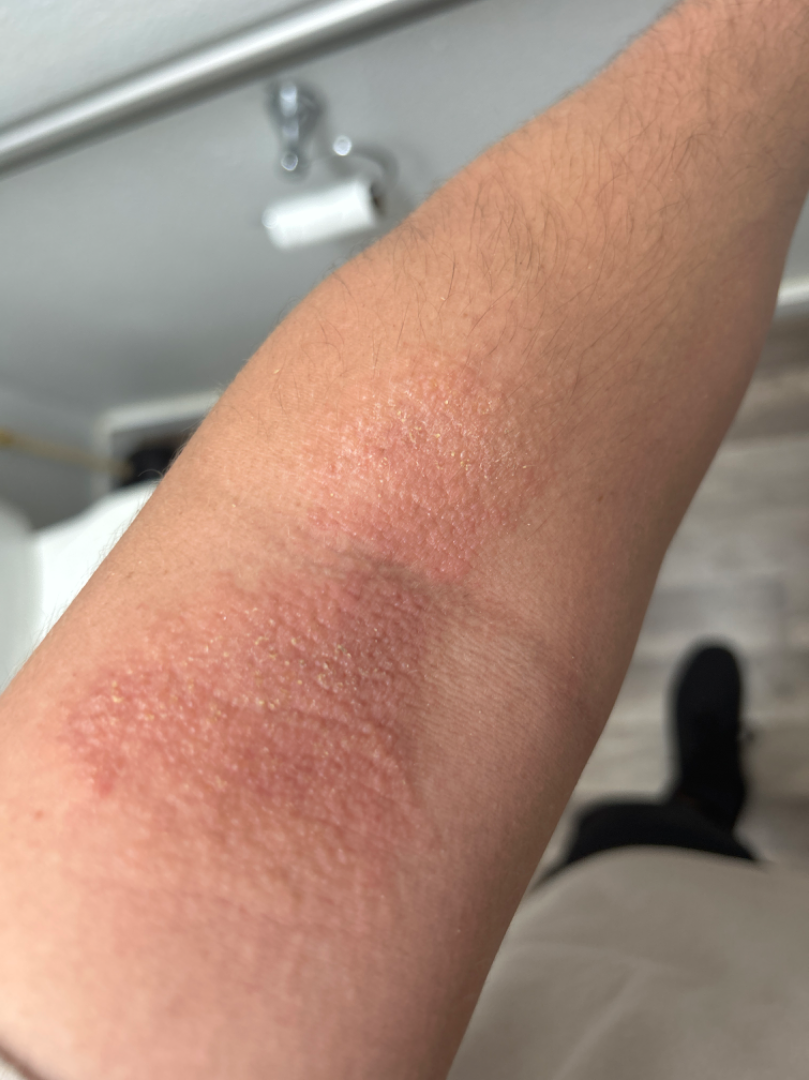differential:
  leading:
    - Lichen Simplex Chronicus
  considered:
    - Psoriasis